The patient also reports joint pain and fatigue; self-categorized by the patient as a pigmentary problem; Fitzpatrick phototype I; the photograph was taken at a distance; the patient is female; symptoms reported: bothersome appearance and enlargement; the condition has been present for more than one year; the affected area is the top or side of the foot, arm and palm — 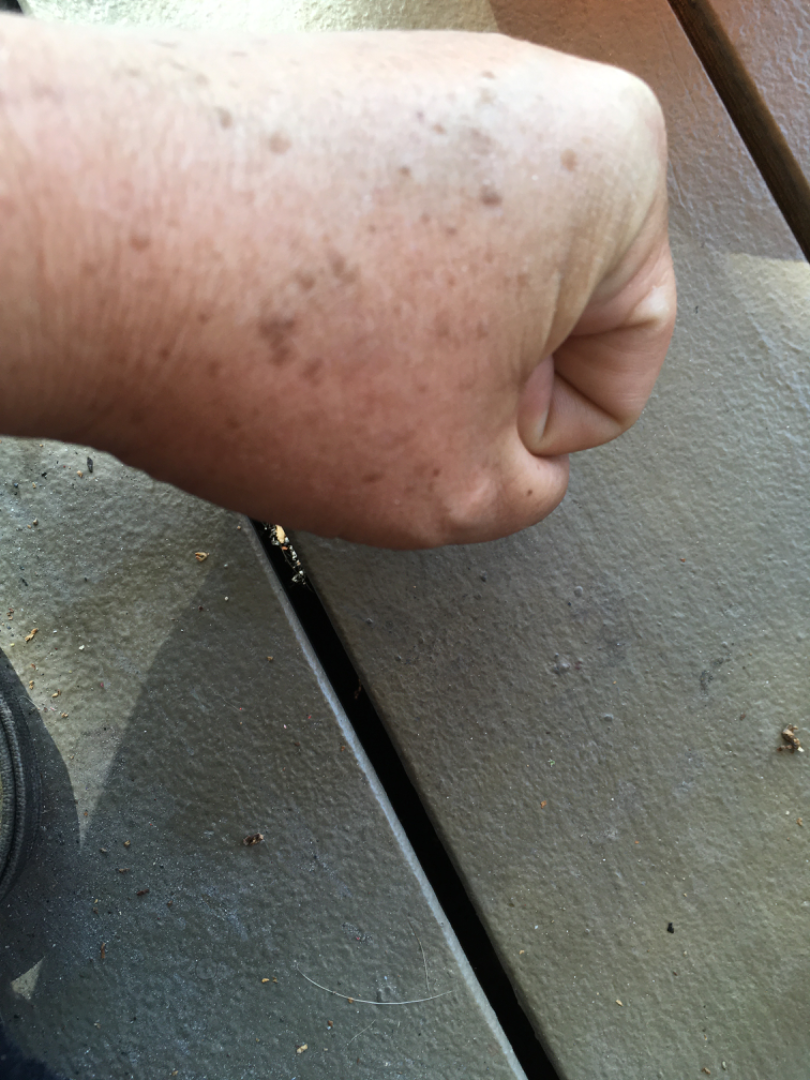The leading consideration is SK/ISK; an alternative is Lentigo.